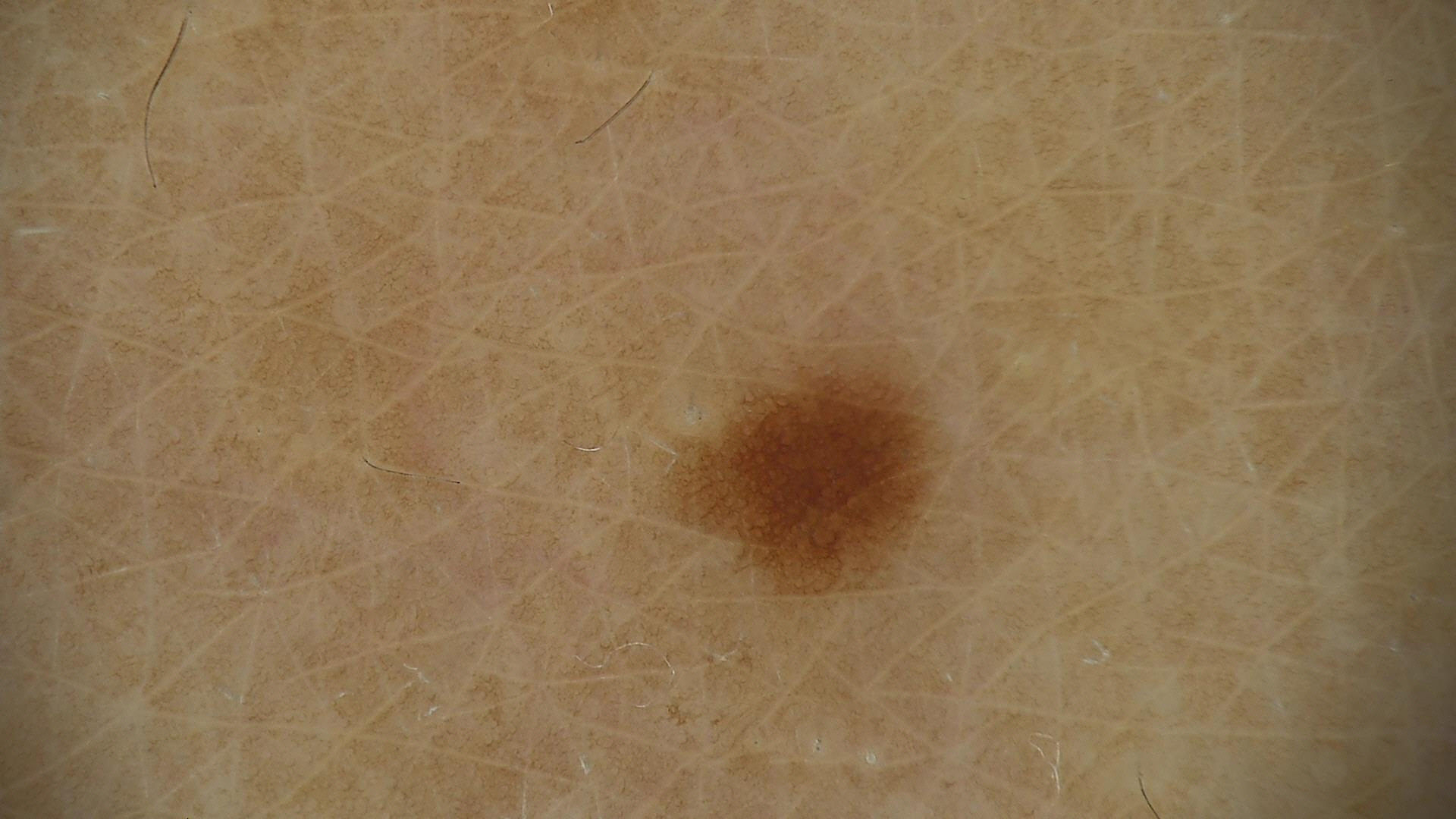label: dysplastic junctional nevus (expert consensus).